A subject aged 34. A clinical close-up photograph of a skin lesion.
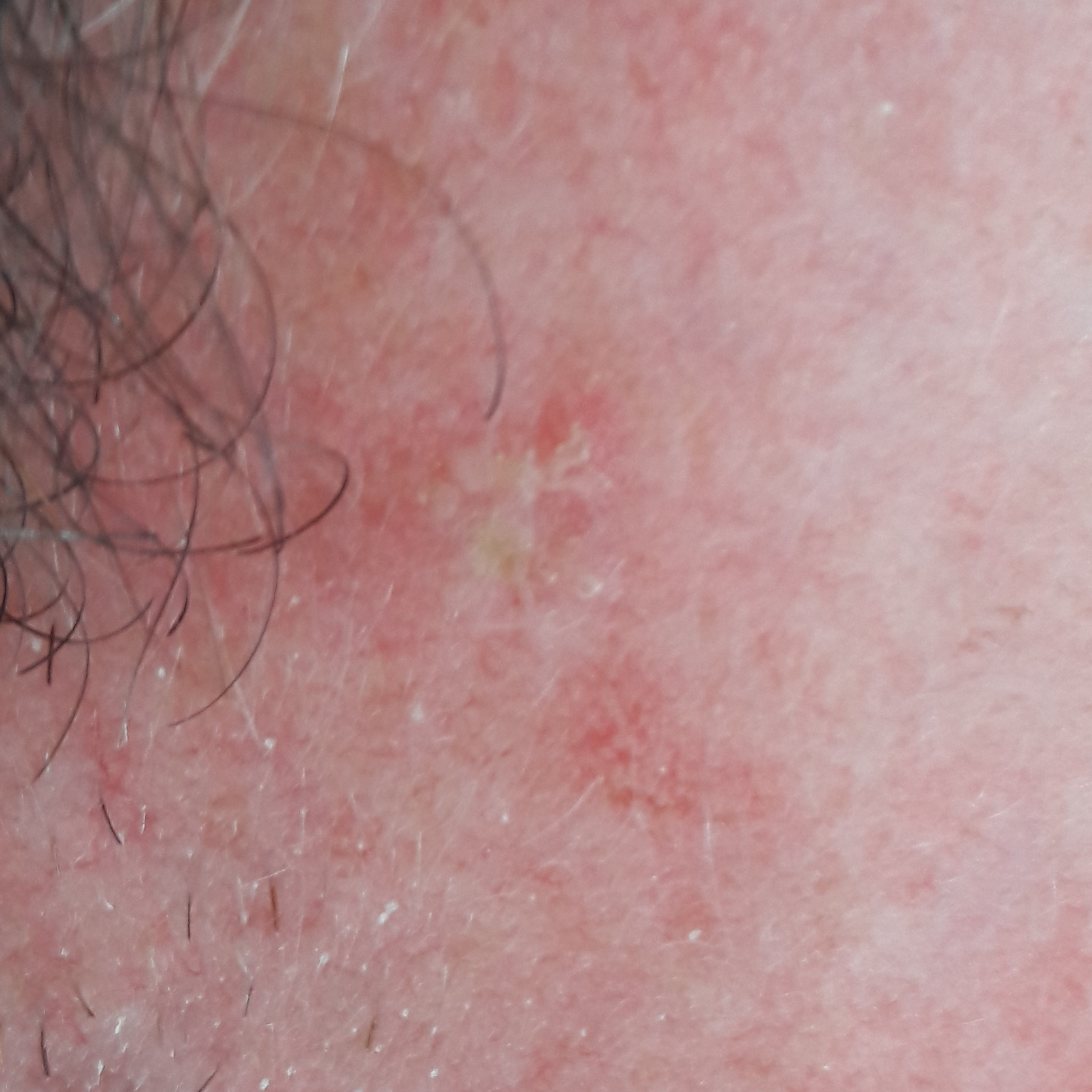Q: Where on the body is the lesion?
A: the face
Q: What is the diagnosis?
A: actinic keratosis (clinical consensus)